A dermoscopic image of a skin lesion; a female patient aged 58 to 62: 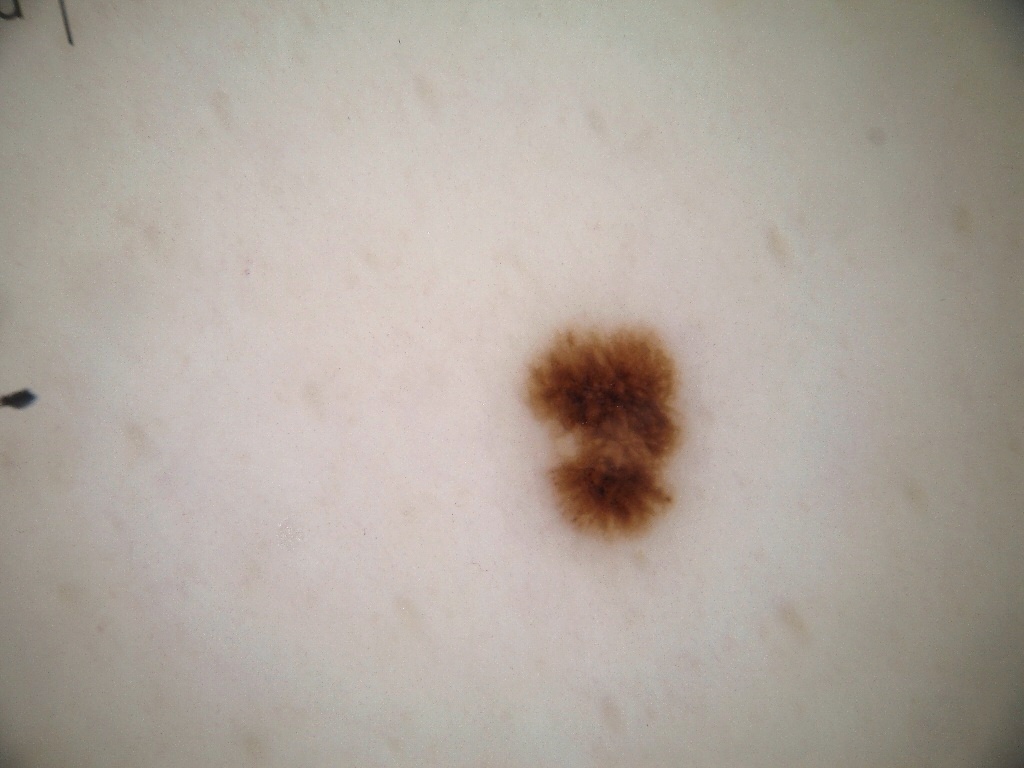{
  "lesion_extent": {
    "approx_field_fraction_pct": 3
  },
  "dermoscopic_features": {
    "present": [],
    "absent": [
      "milia-like cysts",
      "negative network",
      "globules",
      "pigment network",
      "streaks"
    ]
  },
  "lesion_location": {
    "bbox_xyxy": [
      523,
      326,
      684,
      543
    ]
  },
  "diagnosis": {
    "name": "melanoma",
    "malignancy": "malignant",
    "lineage": "melanocytic",
    "provenance": "histopathology"
  }
}